This image was taken at a distance. Texture is reported as rough or flaky. The patient described the issue as a rash. The condition has been present for about one day: 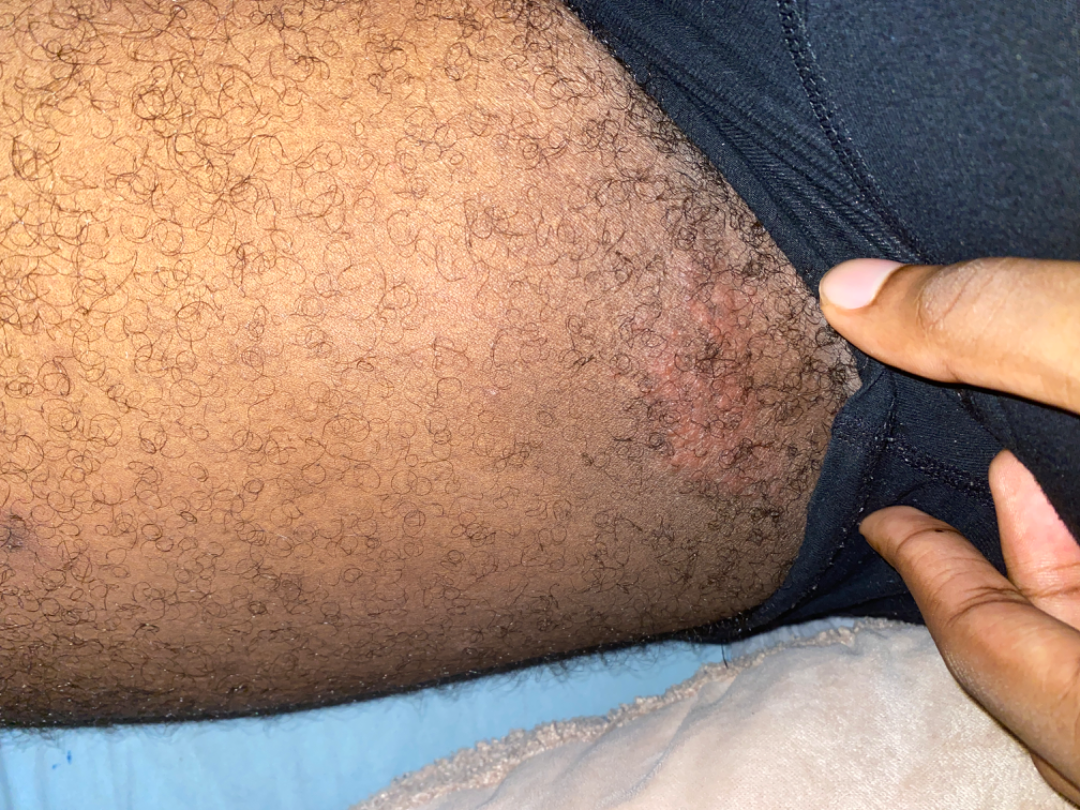Q: What was the assessment?
A: indeterminate from the photograph